The lesion involves the head or neck, the subject is a female aged 18–29, no relevant systemic symptoms, the photograph is a close-up of the affected area, the condition has been present for about one day, the lesion is associated with itching and bothersome appearance, the patient considered this acne — 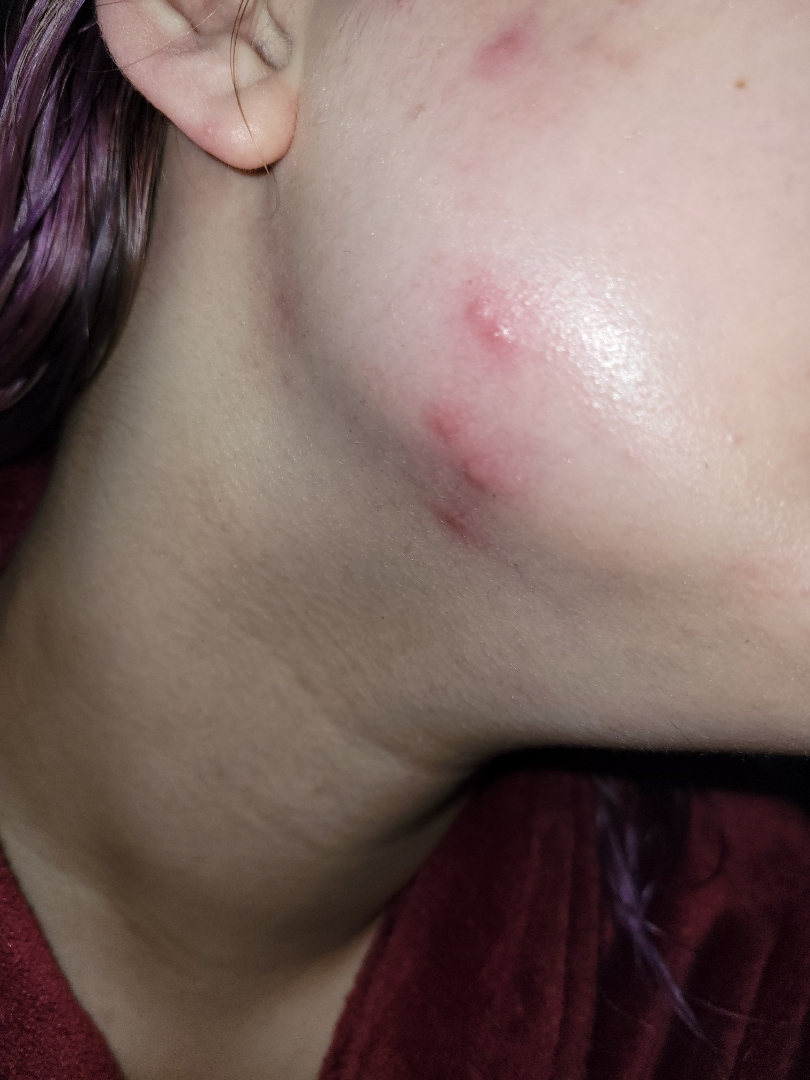On photographic review by a dermatologist, Acne and Molluscum Contagiosum were considered with similar weight.